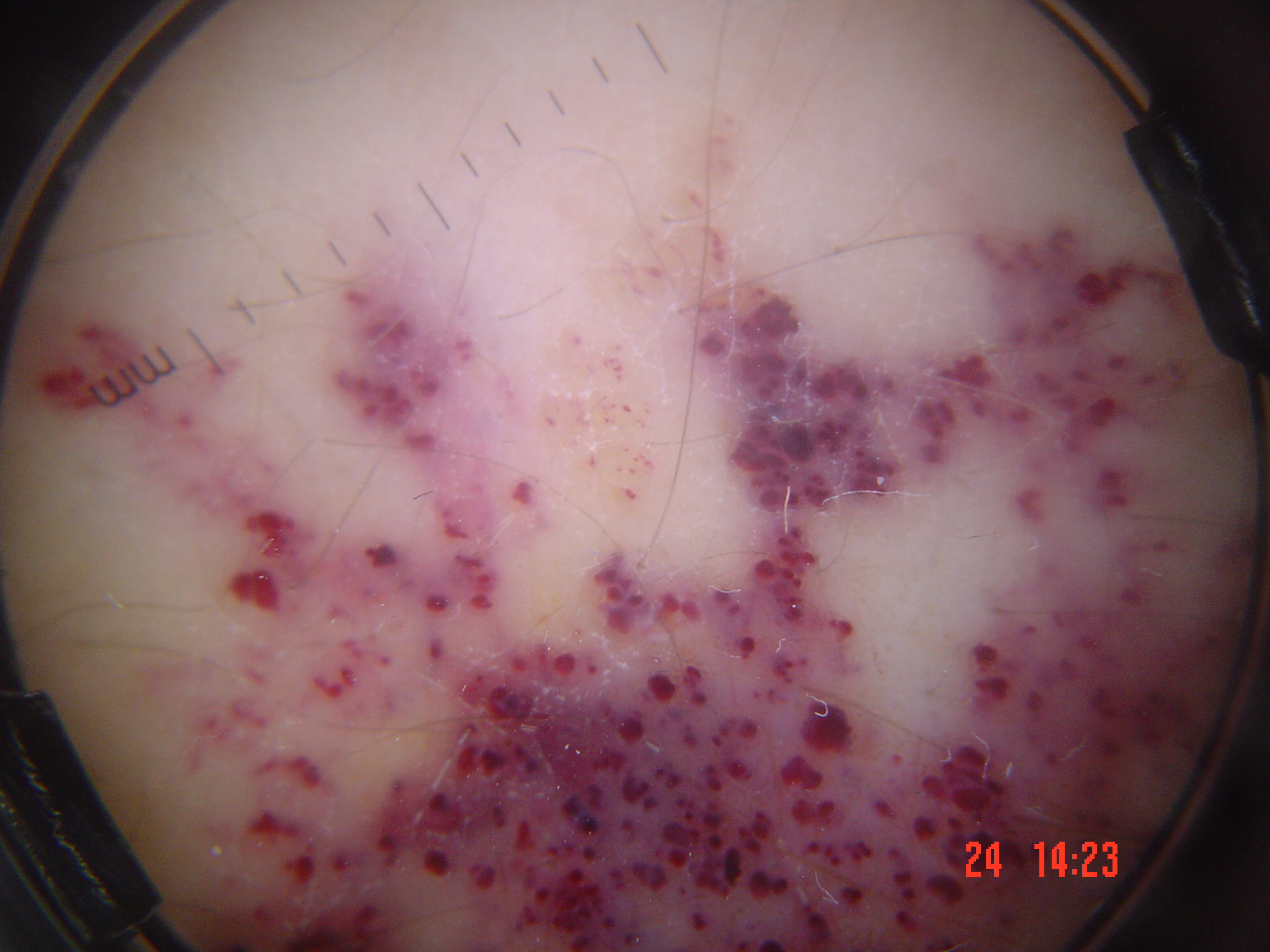| key | value |
|---|---|
| modality | dermatoscopy |
| category | vascular |
| diagnostic label | hemangioma (expert consensus) |